Contact-polarized dermoscopy of a skin lesion — 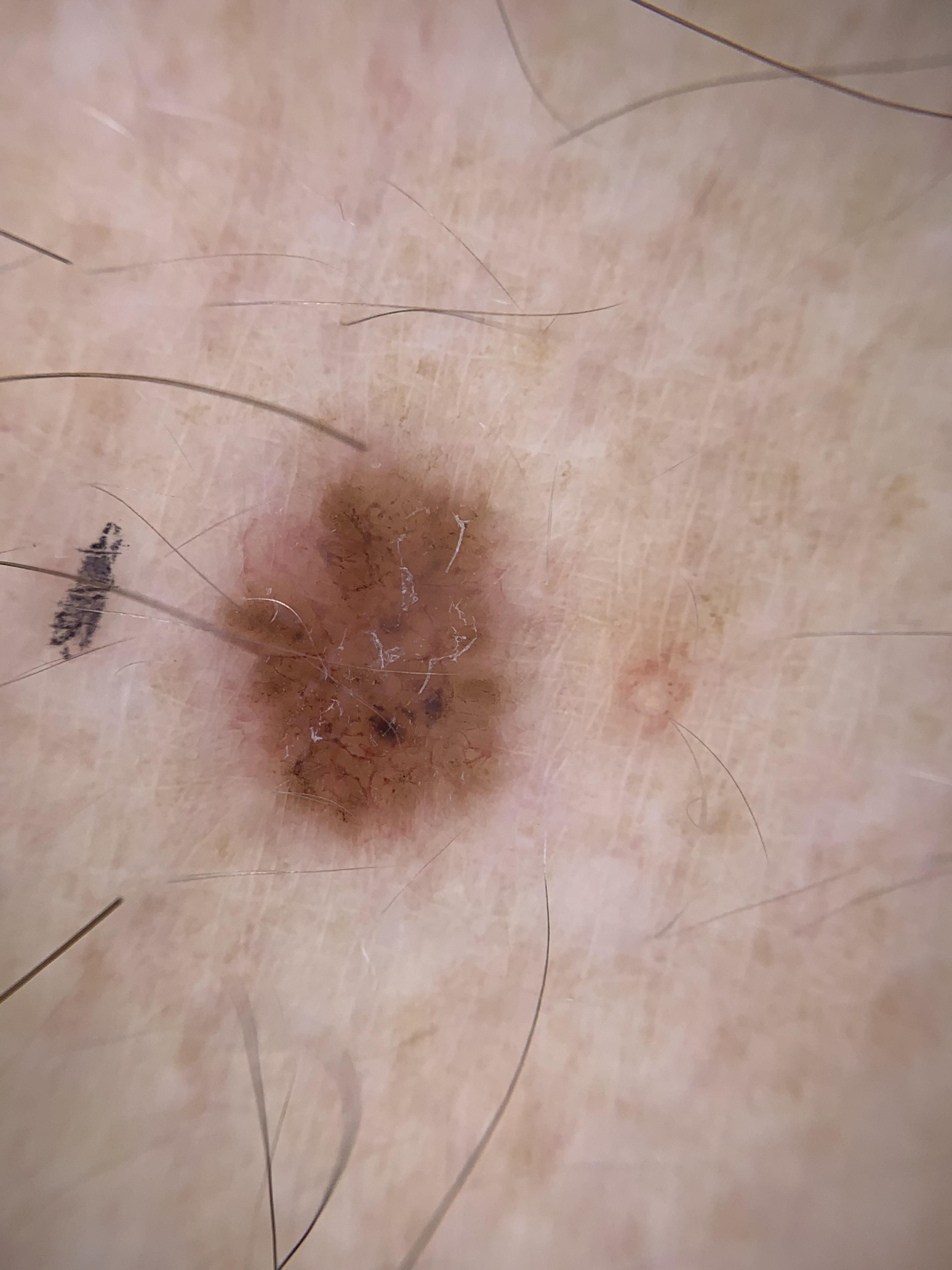The biopsy diagnosis was a lesion of adnexal (follicular) origin — a basal cell carcinoma.